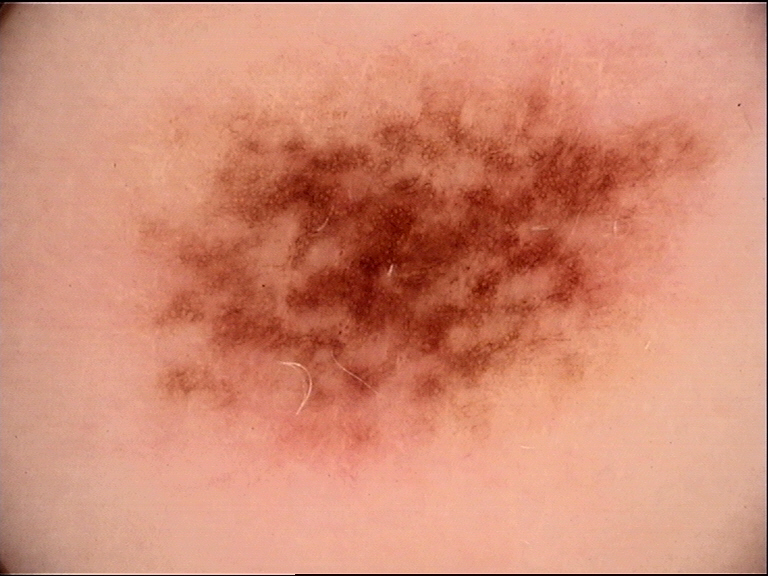Classified as a dysplastic junctional nevus.